A clinical photograph of a skin lesion; a female subject 59 years of age; imaged for a research study, with no referral diagnosis recorded; a moderate number of moles by the patient's own estimate; the patient says their skin reddens with sun exposure: 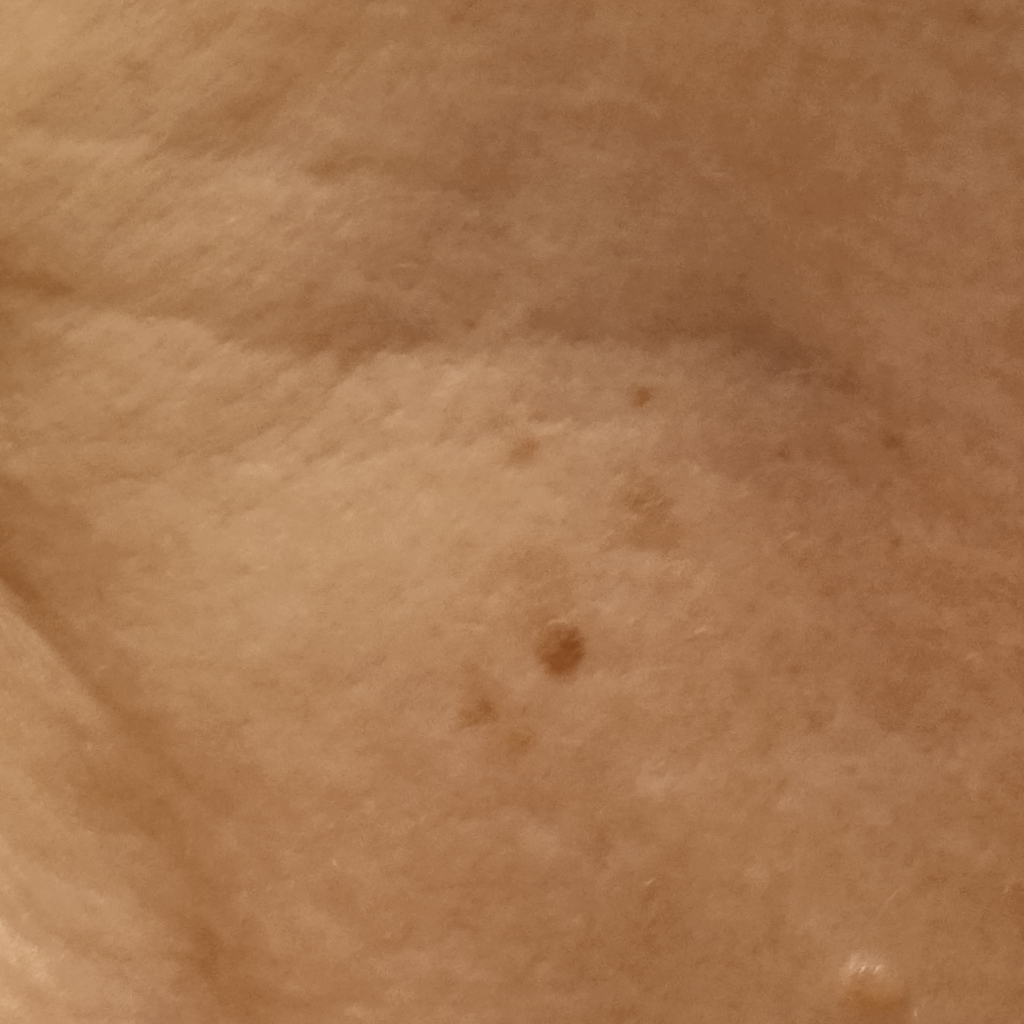{
  "lesion_size": {
    "diameter_mm": 2.2
  },
  "diagnosis": {
    "name": "seborrheic keratosis",
    "malignancy": "benign"
  }
}